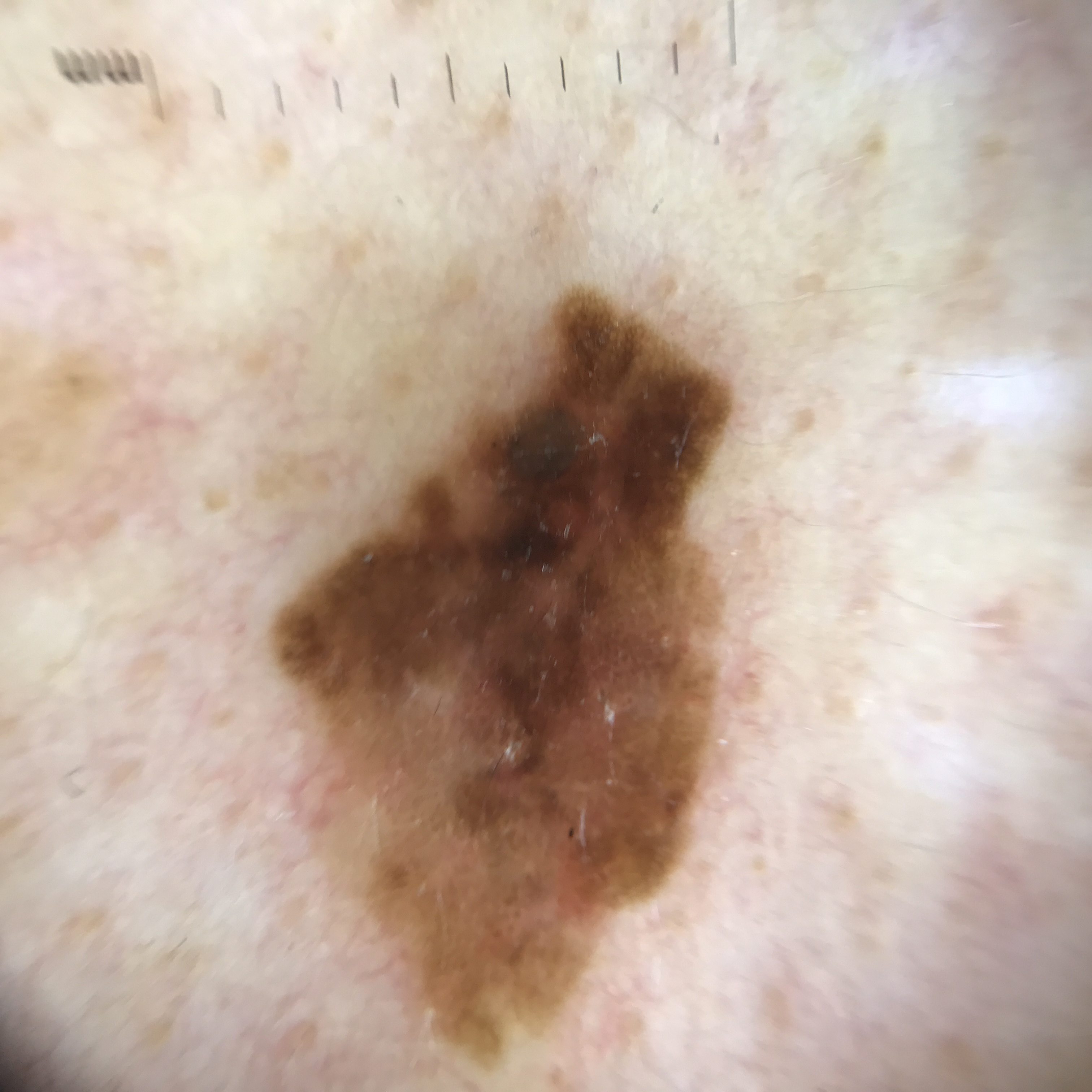pathology — melanoma (biopsy-proven).